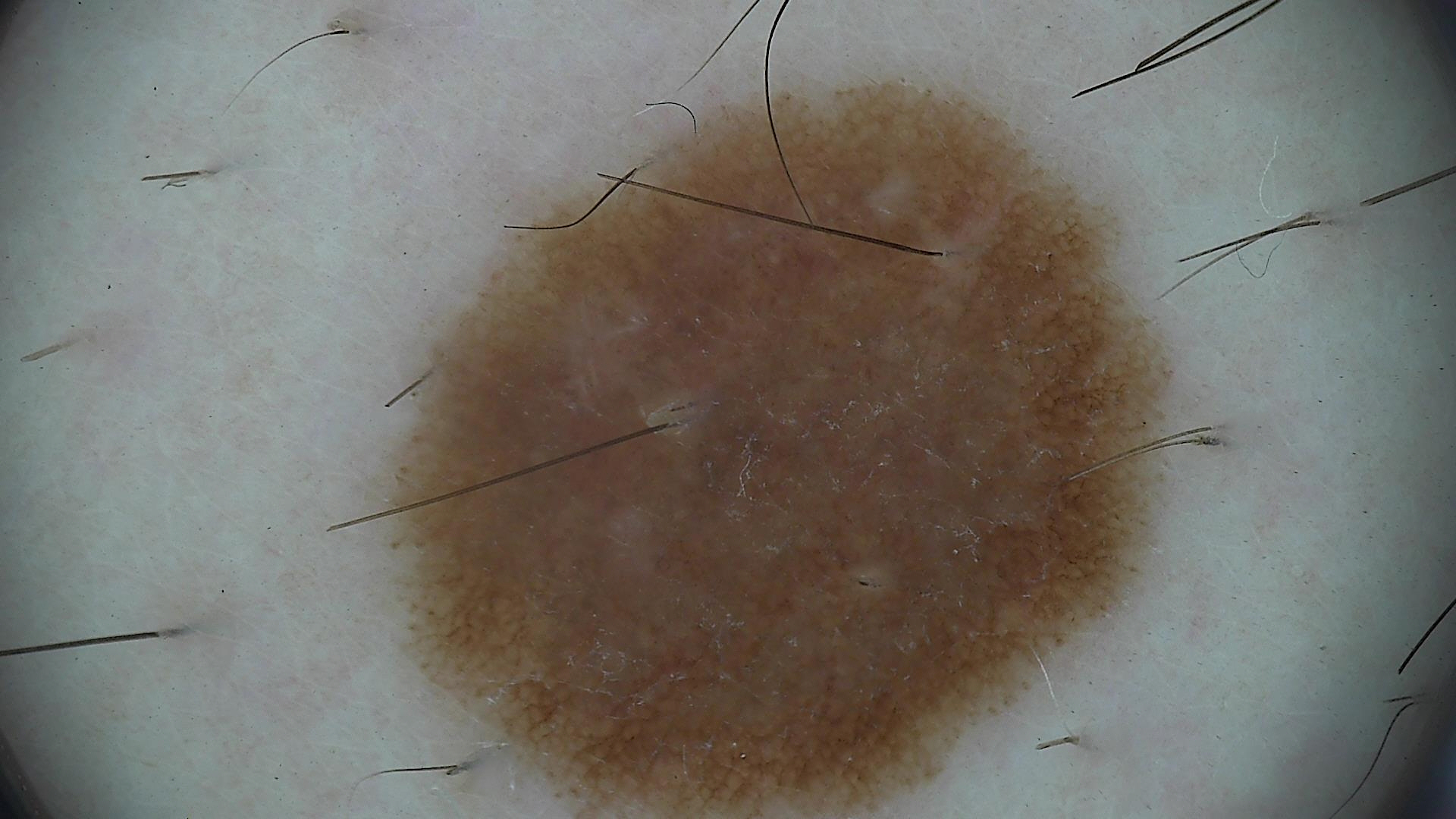class: dysplastic junctional nevus (expert consensus)